A skin lesion imaged with a dermatoscope.
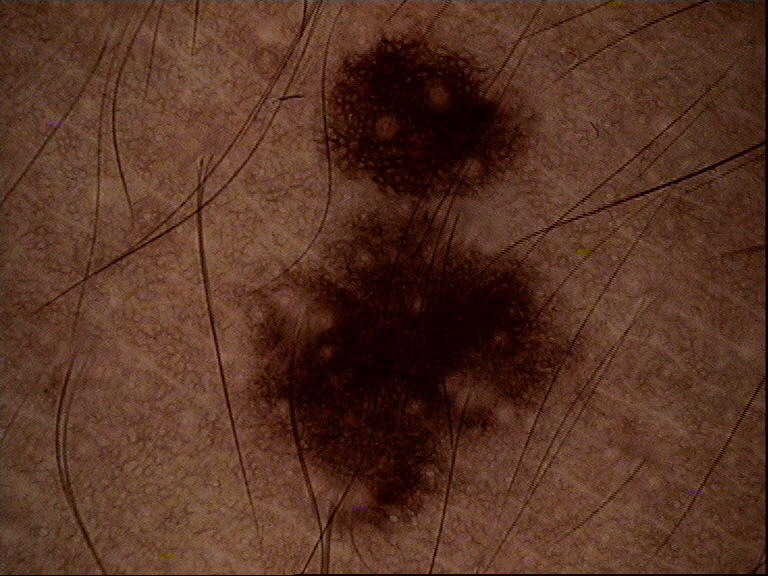Diagnosed as a benign lesion — a dysplastic junctional nevus.